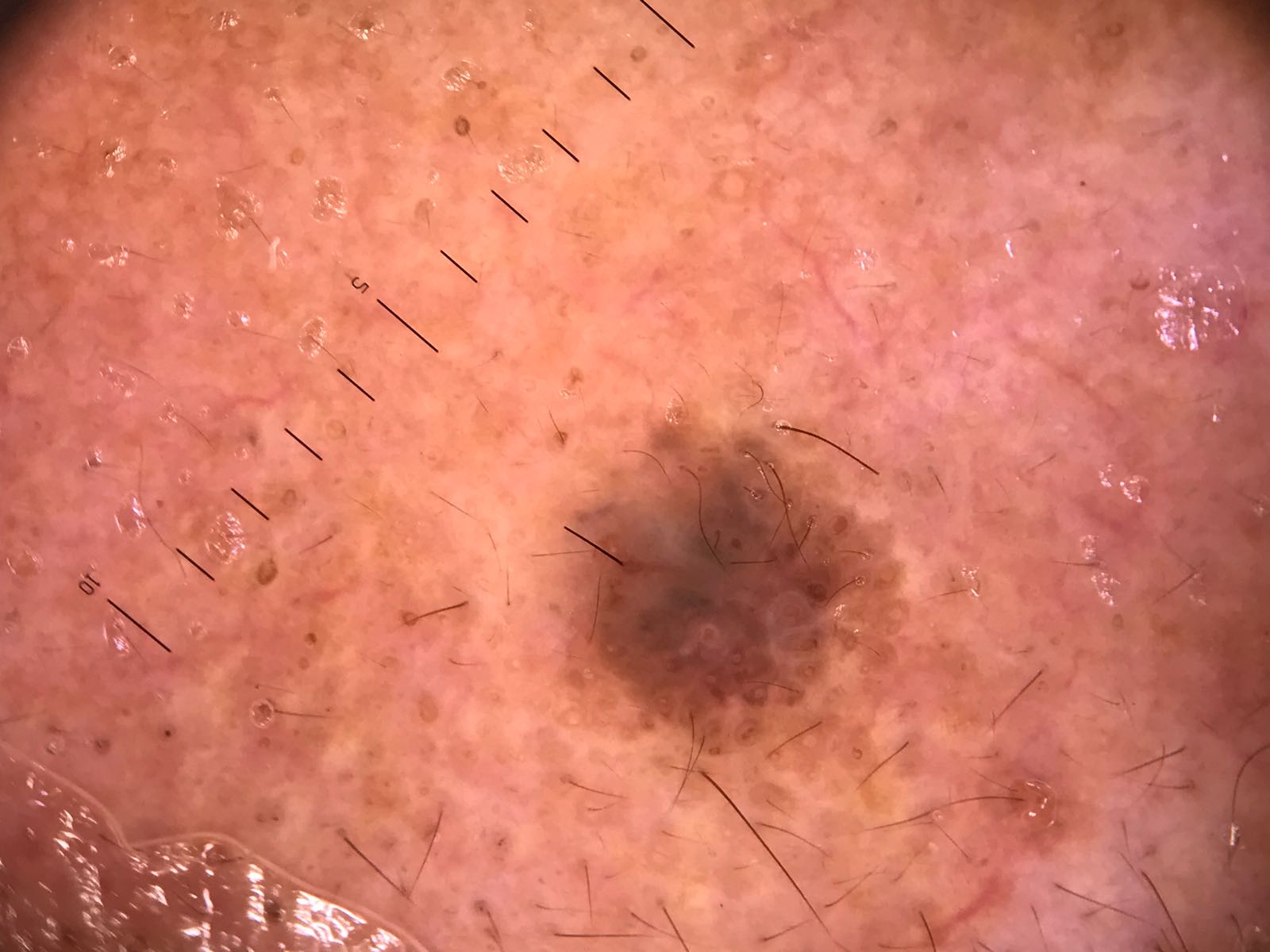| key | value |
|---|---|
| class | seborrheic keratosis (expert consensus) |